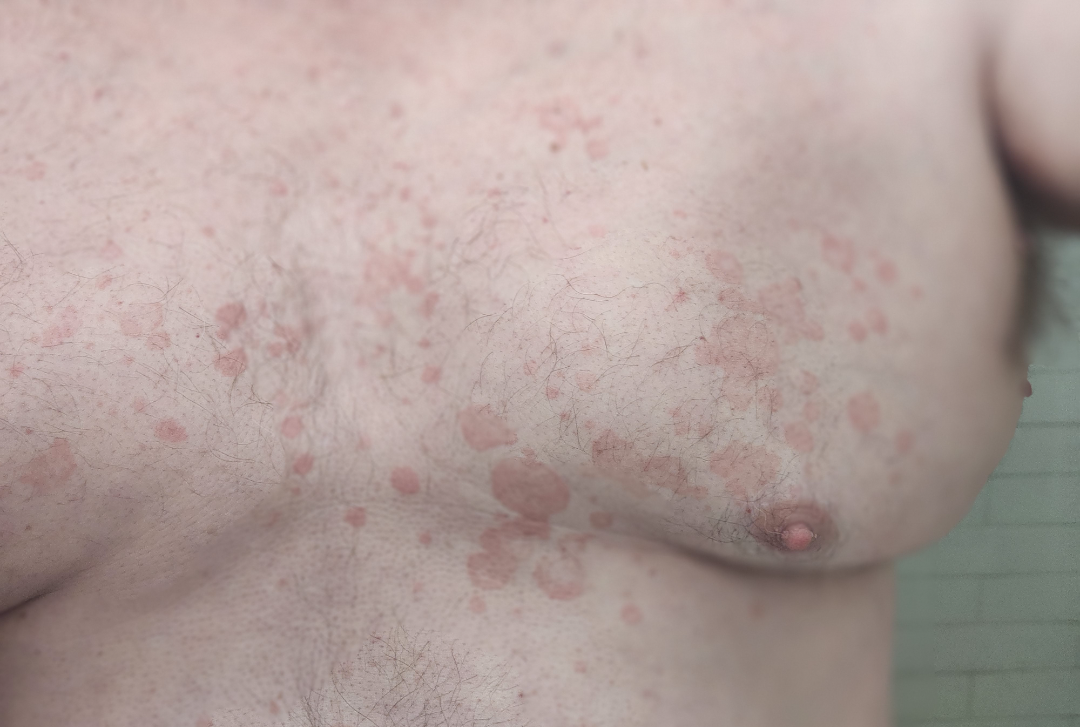The case was indeterminate on photographic review.
The front of the torso is involved.
The patient reports the condition has been present for more than one year.
This image was taken at a distance.
The patient described the issue as skin that appeared healthy to them.
Texture is reported as flat.
The lesion is associated with darkening and bothersome appearance.